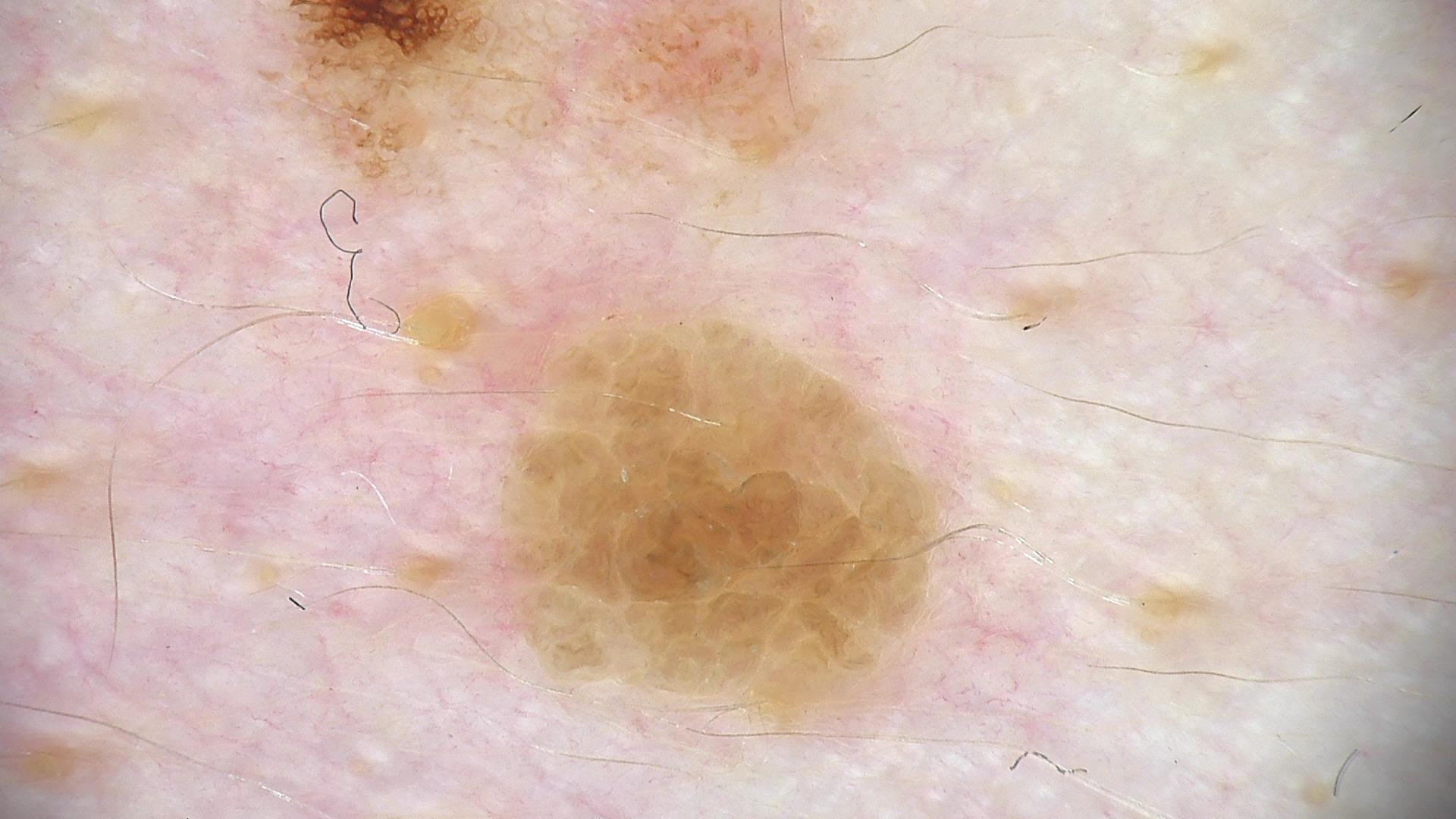assessment: seborrheic keratosis (expert consensus).